Located on the arm; close-up view:
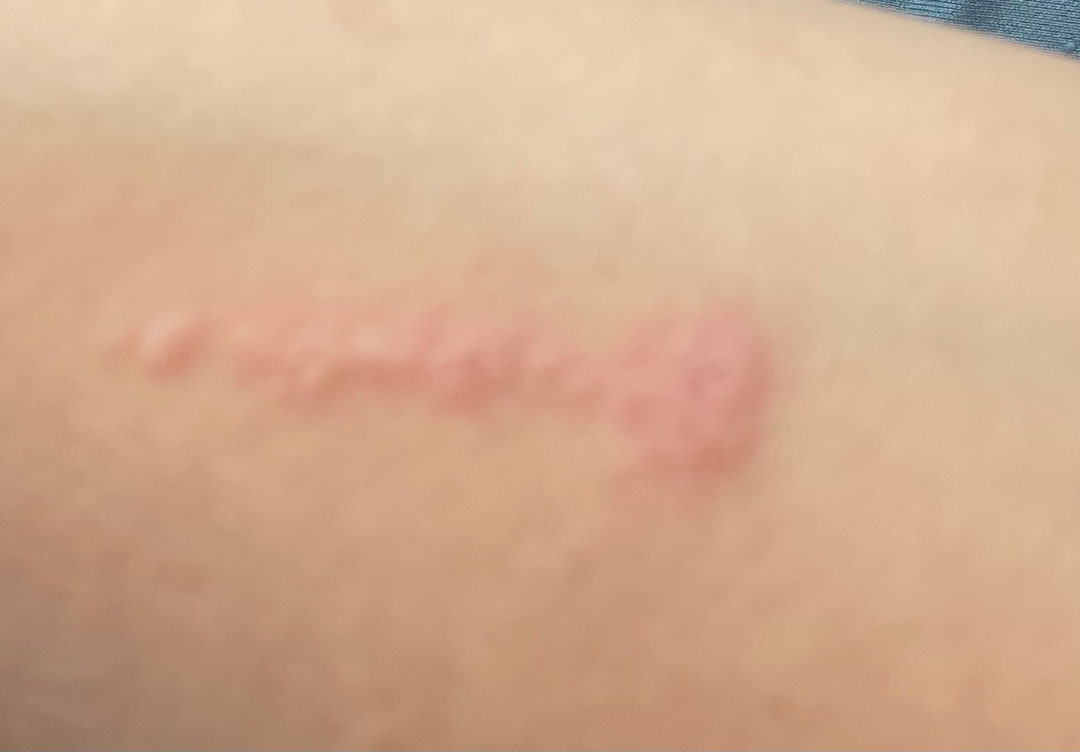| key | value |
|---|---|
| assessment | indeterminate from the photograph |
| self-categorized as | a rash |
| described texture | raised or bumpy |